A skin lesion imaged with a dermatoscope.
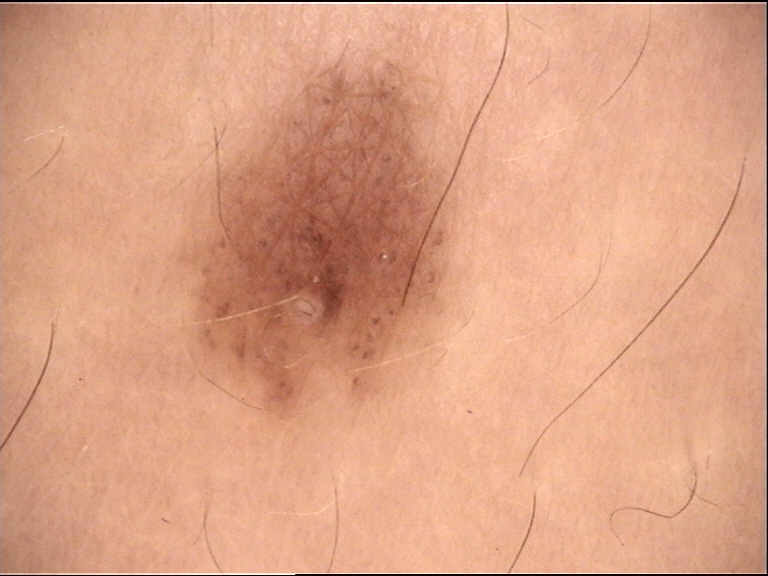Diagnosed as a benign lesion — a dysplastic junctional nevus.